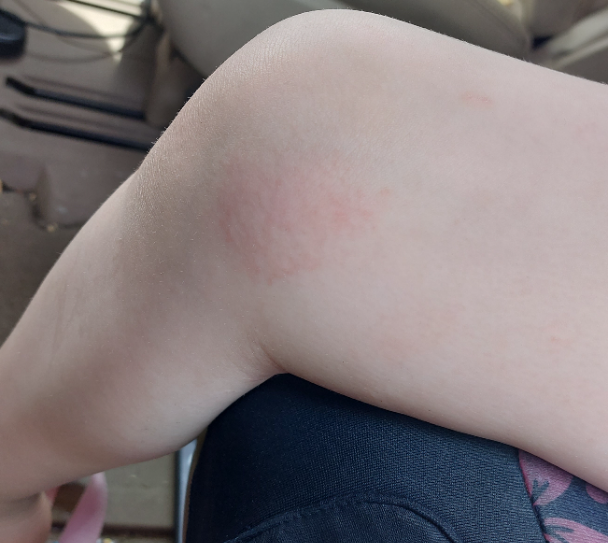– assessment: could not be assessed